A subject in their 50s:
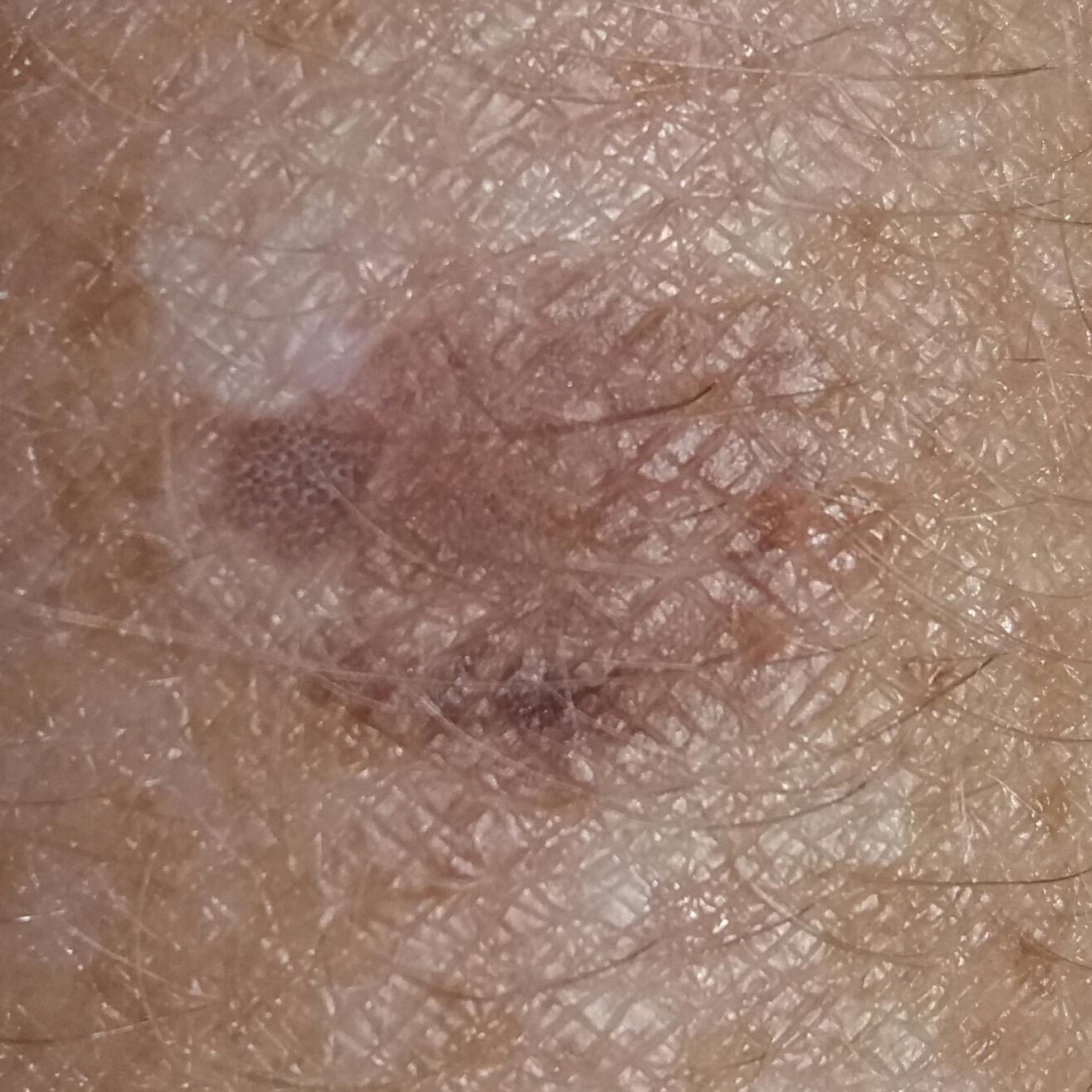The lesion is on a forearm. The patient reports no symptoms. Diagnosed by dermatologist consensus as a benign lesion — a seborrheic keratosis.